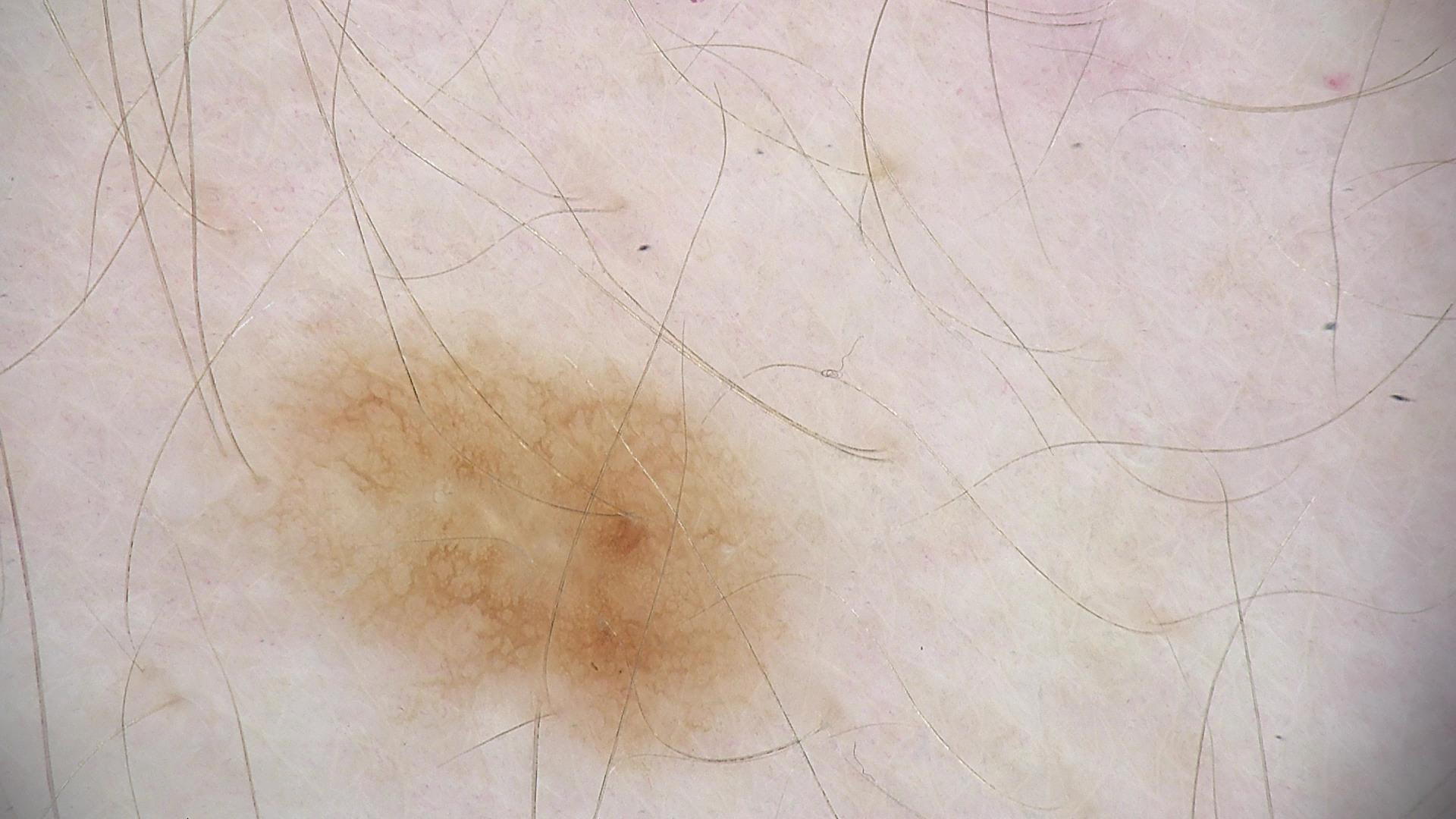Labeled as a dysplastic junctional nevus.